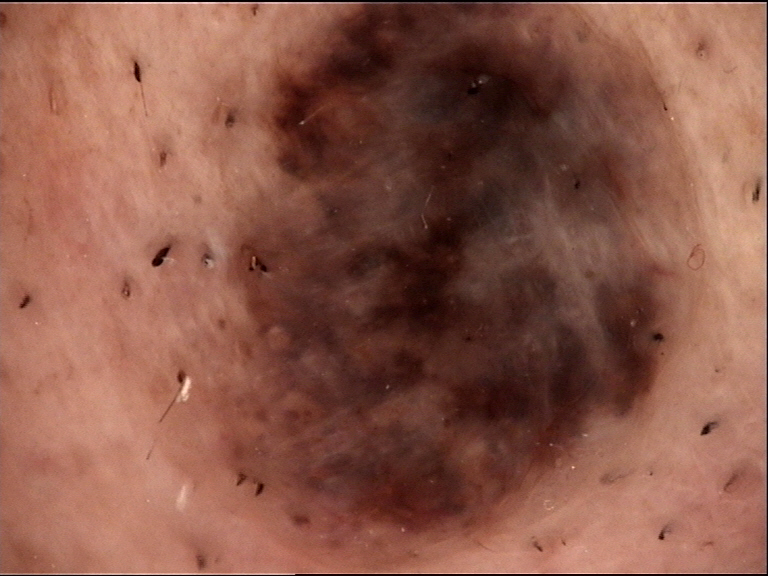Q: What kind of image is this?
A: dermatoscopy
Q: What is this lesion?
A: congenital dysplastic compound nevus (expert consensus)